Dermoscopy of a skin lesion:
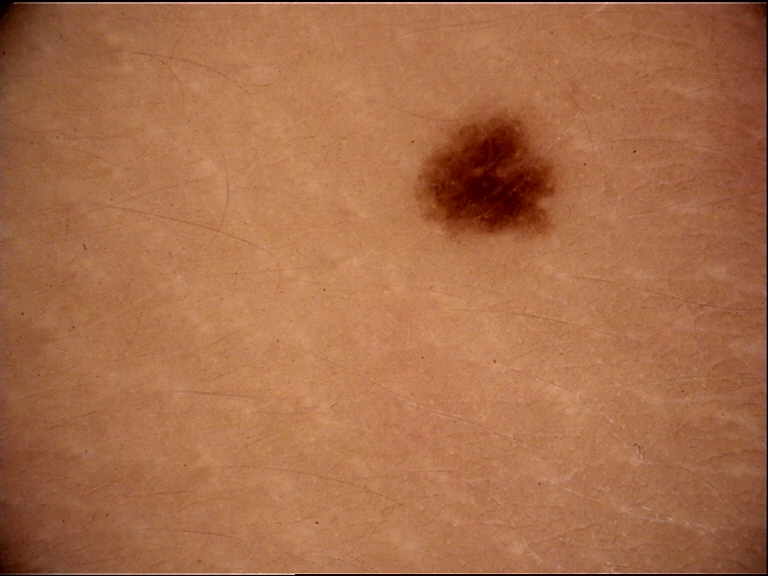diagnostic label: junctional nevus (expert consensus).